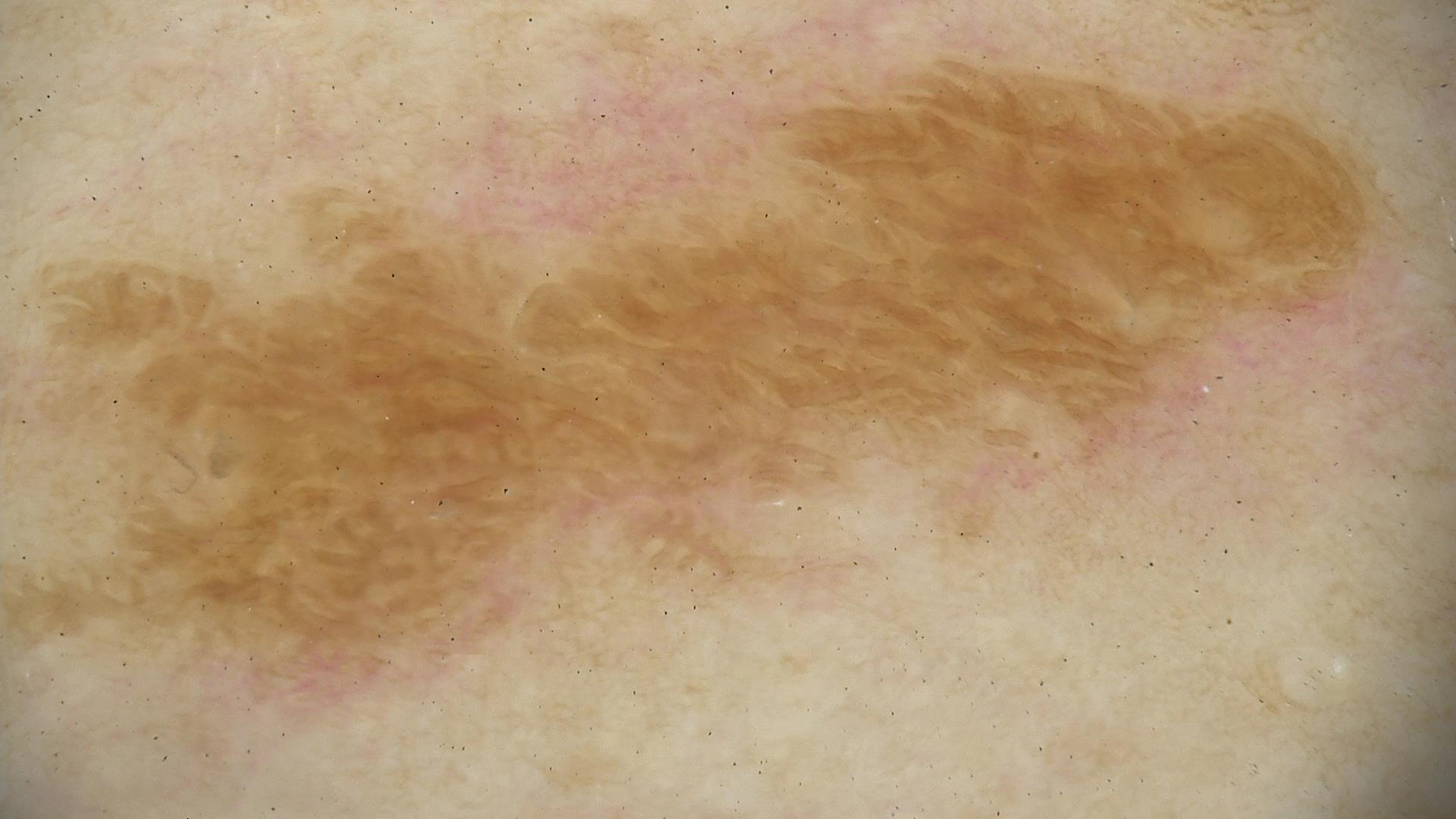image type — dermatoscopy; lesion type — keratinocytic; class — seborrheic keratosis (expert consensus).